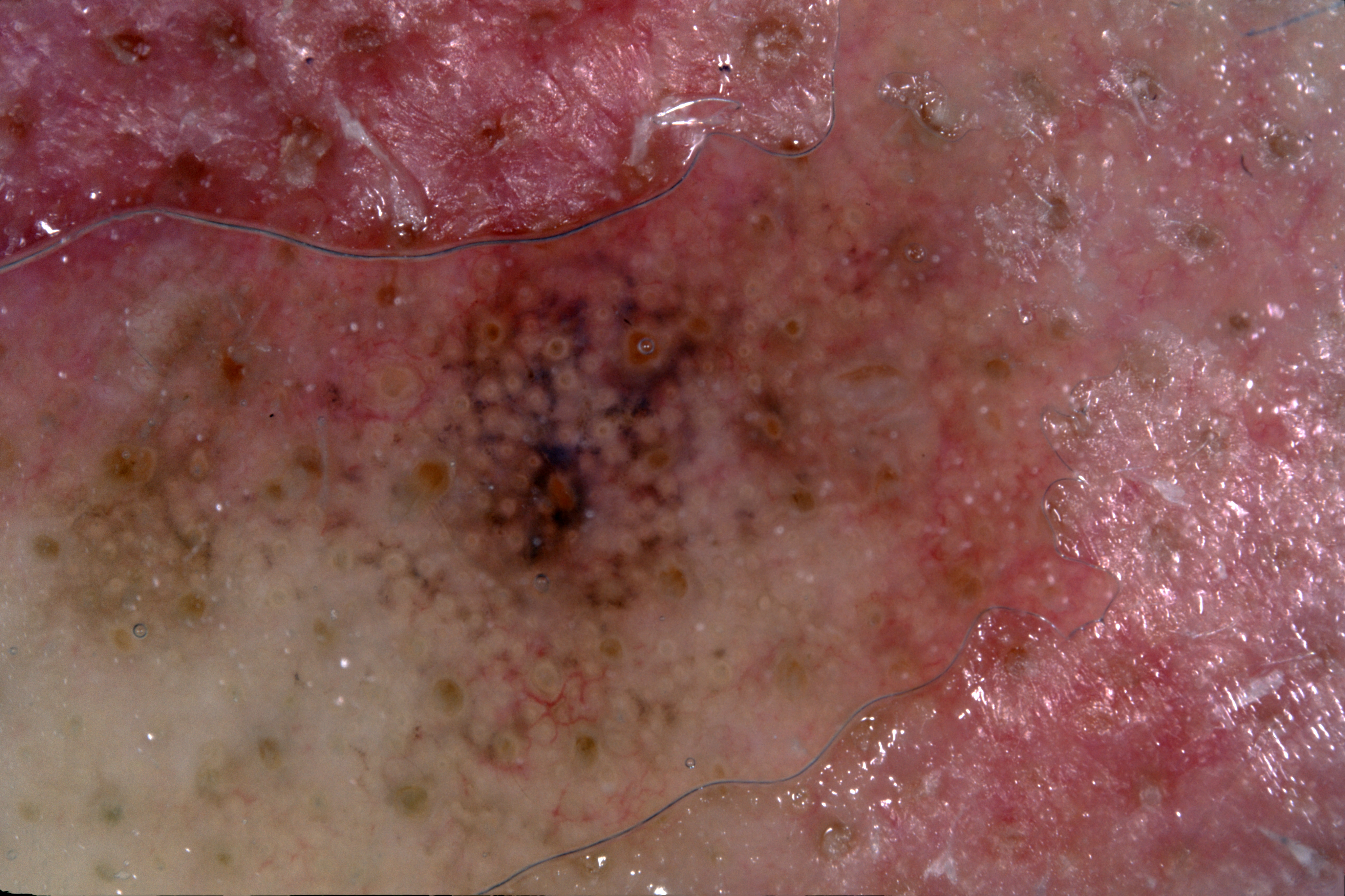Q: What kind of image is this?
A: dermoscopy of a skin lesion
Q: Who is the patient?
A: male, about 60 years old
Q: How much of the field does the lesion occupy?
A: large
Q: Where is the lesion in the image?
A: box(0, 77, 1176, 868)
Q: What is notable about the lesion's margin?
A: reaches the image border
Q: What dermoscopic features are not present?
A: pigment network, milia-like cysts, streaks, and negative network
Q: What did the assessment conclude?
A: a melanoma, a skin cancer